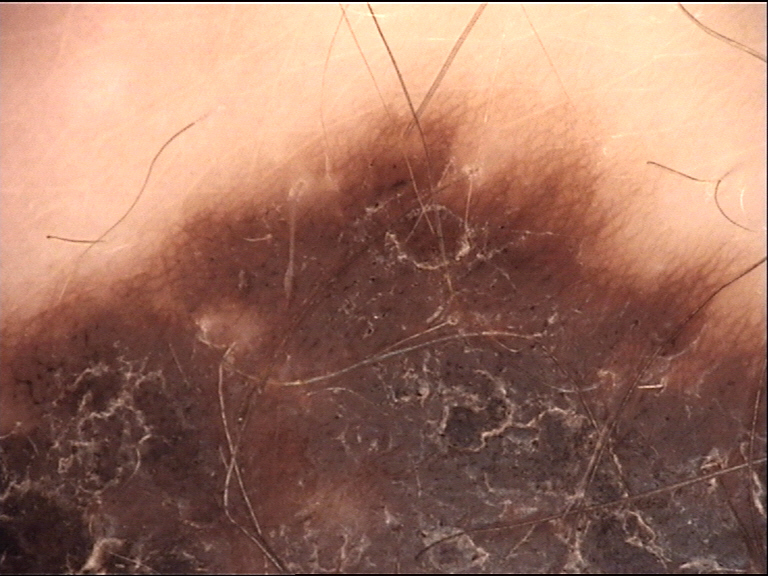image = dermatoscopy | lesion type = banal | diagnosis = congenital compound nevus (expert consensus).